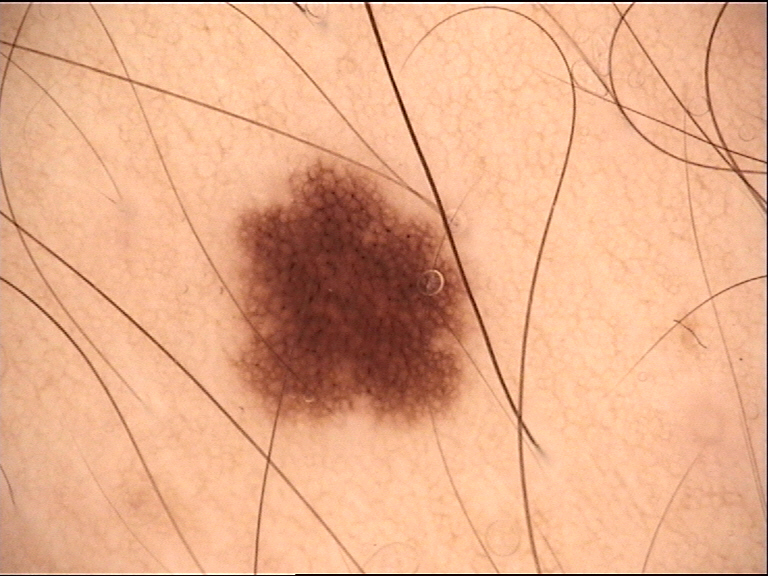A dermoscopy image of a single skin lesion.
Diagnosed as a junctional nevus.